The lesion involves the leg · a close-up photograph: 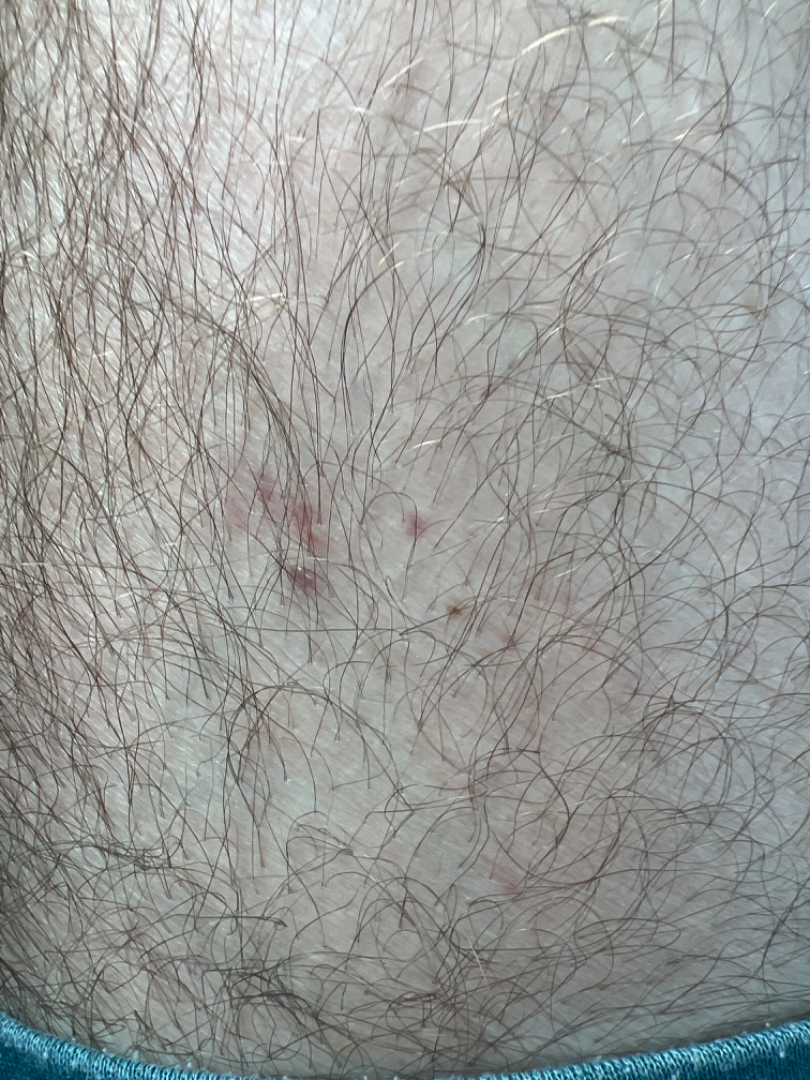Q: Could the case be diagnosed?
A: could not be assessed